An image taken at an angle · the lesion involves the head or neck · female contributor, age 30–39.
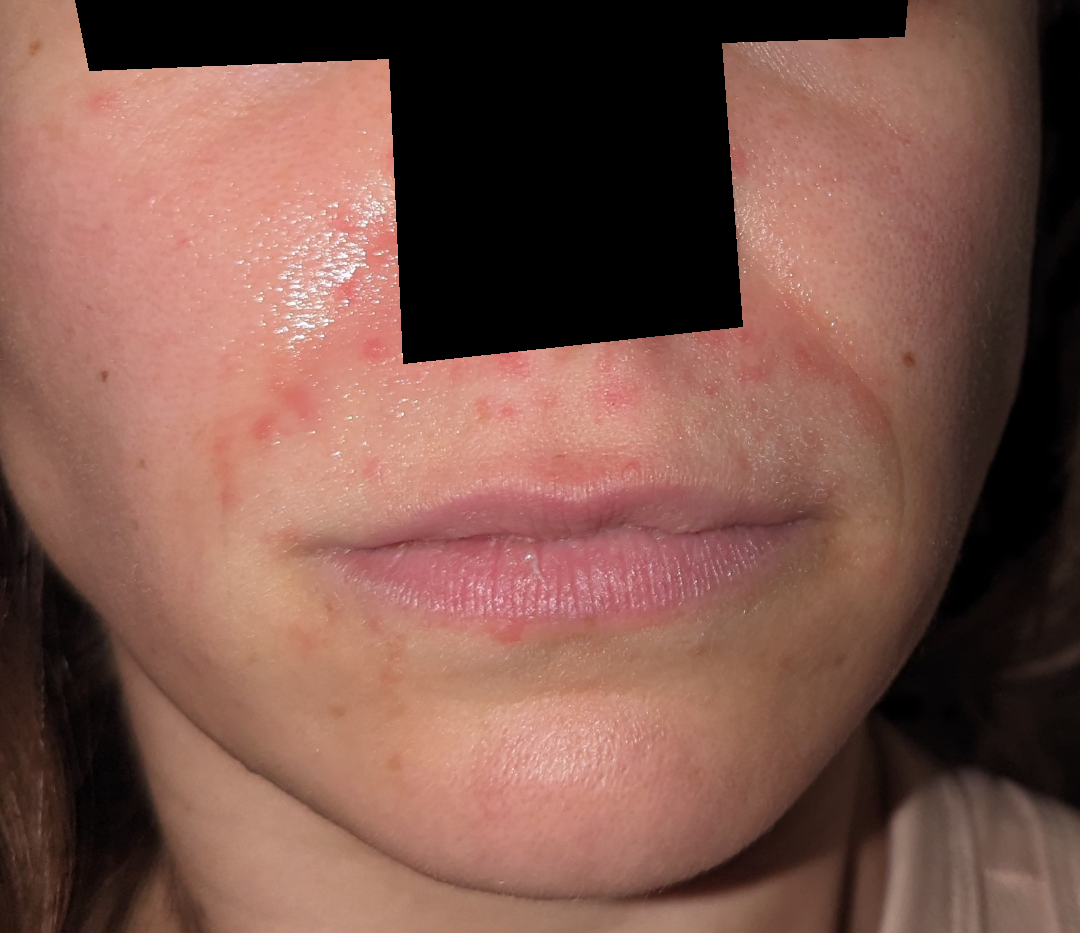assessment = ungradable on photographic review
self-categorized as = a rash
systemic symptoms = fatigue
present for = one to three months
texture = rough or flaky and raised or bumpy
symptoms = burning, bothersome appearance and pain